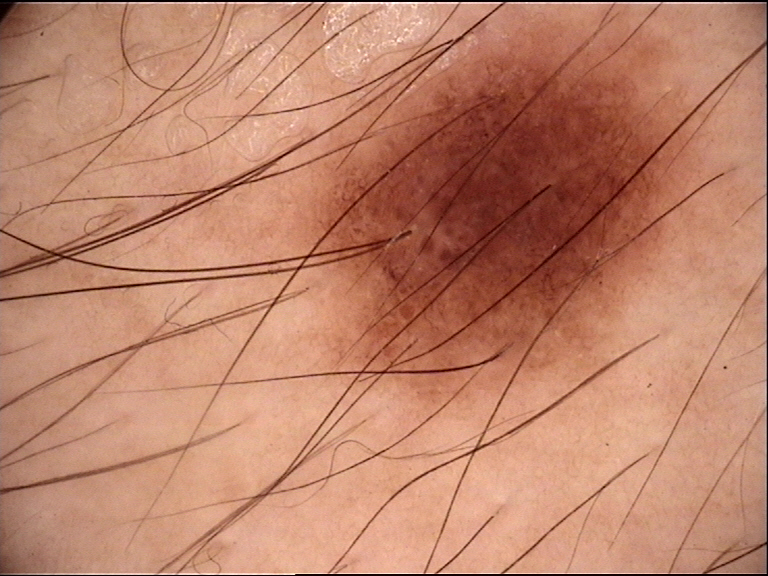A dermoscopic image of a skin lesion.
The architecture is that of a banal lesion.
Diagnosed as a junctional nevus.